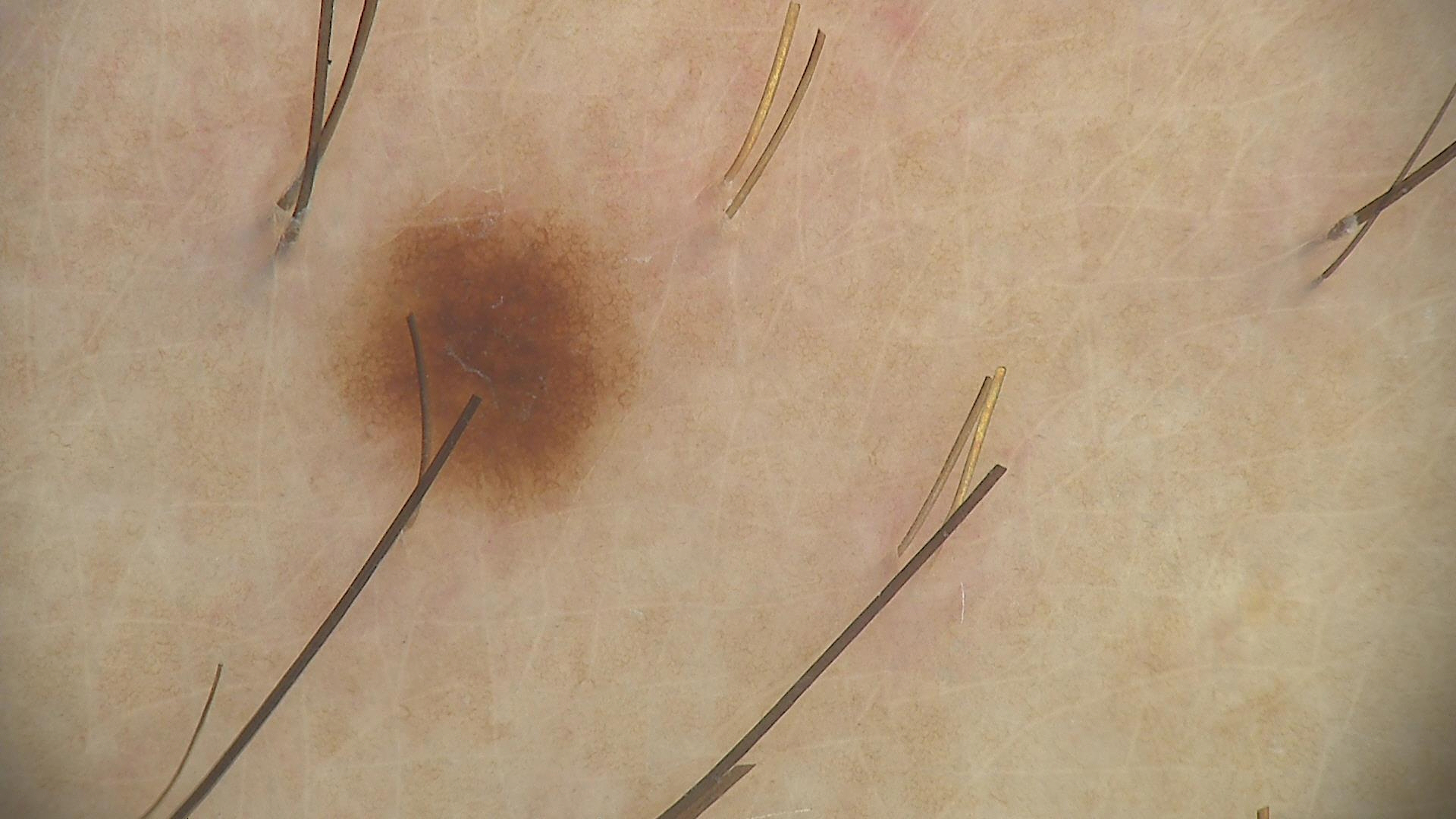Dermoscopy of a skin lesion. Consistent with a banal lesion — a junctional nevus.